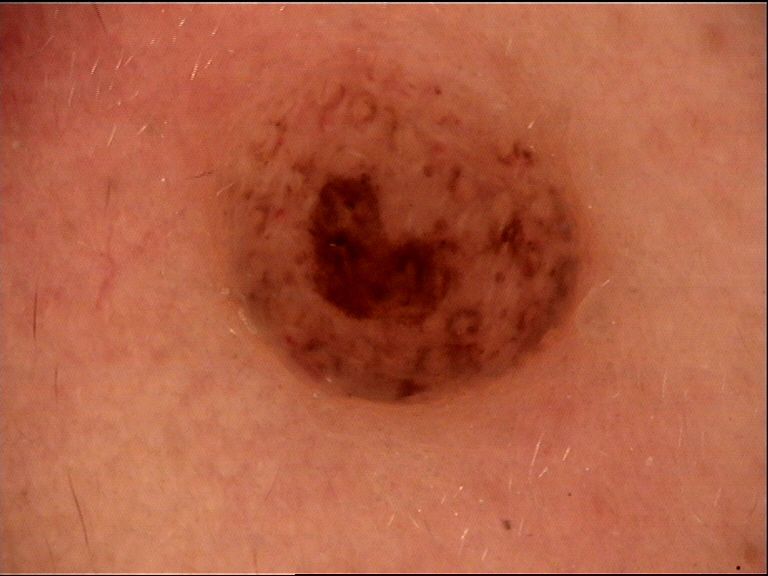Dermoscopy of a skin lesion. Consistent with a banal lesion — a dermal nevus.